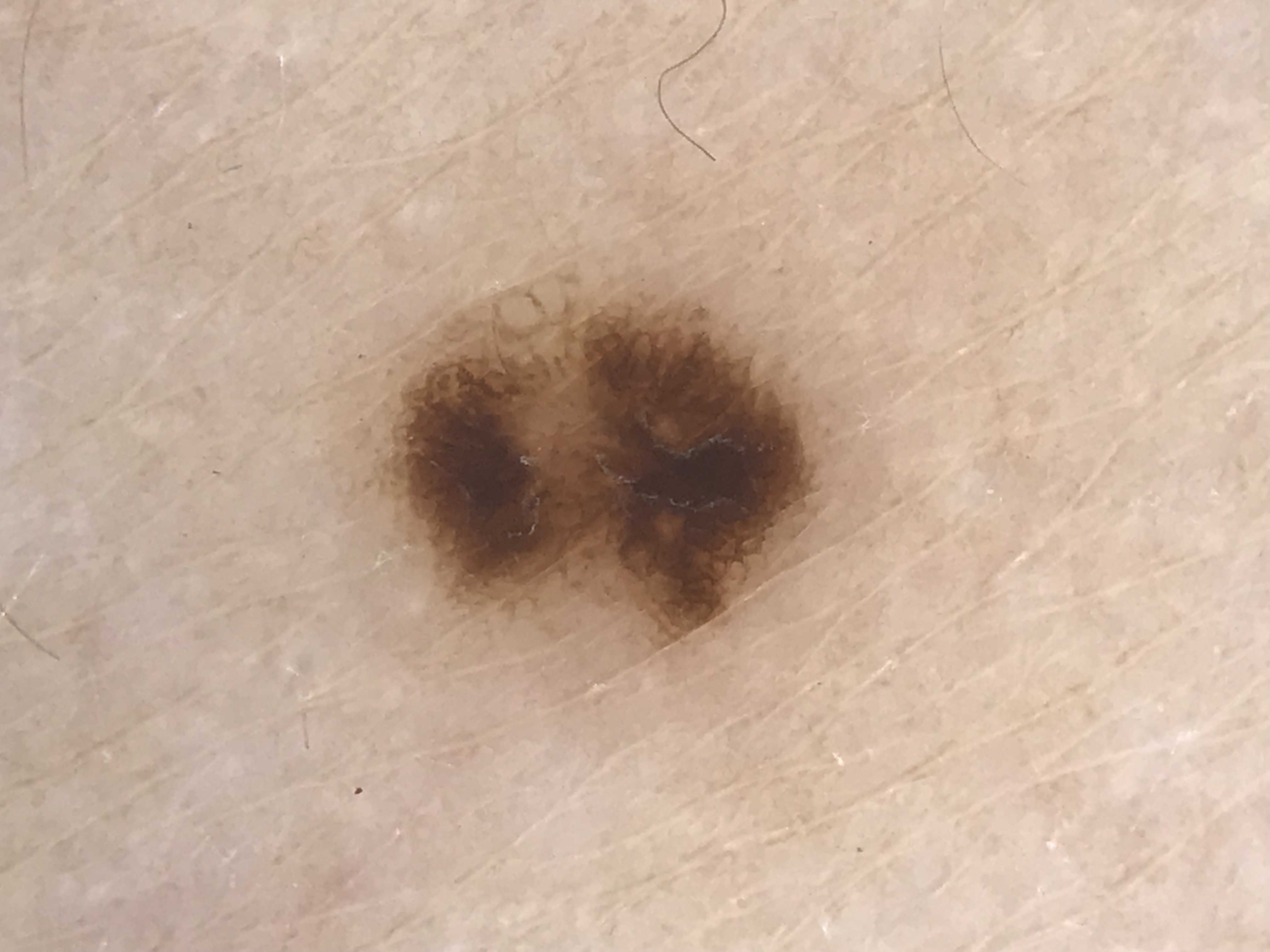modality=dermoscopy; diagnosis=dysplastic junctional nevus (expert consensus).